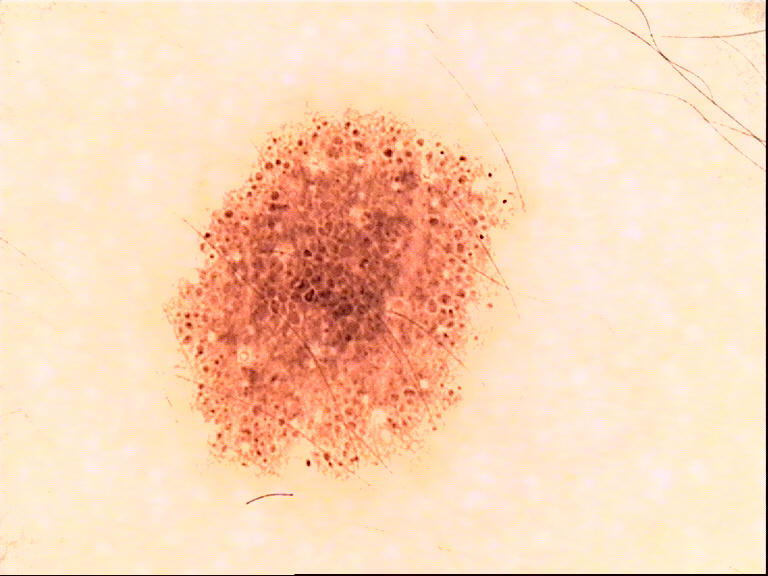Labeled as a dysplastic compound nevus.